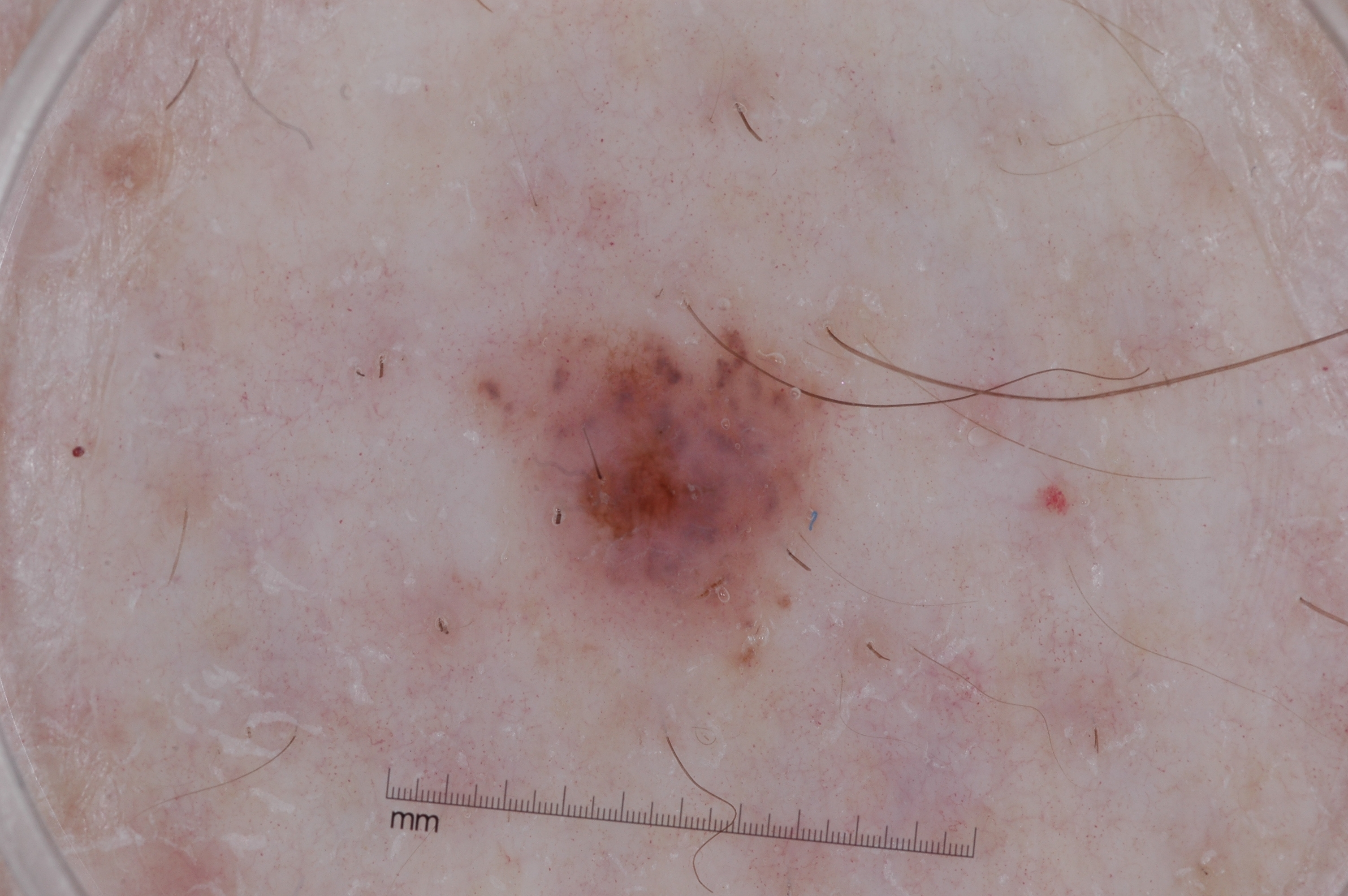The patient is a female aged 58 to 62.
A dermoscopic view of a skin lesion.
Dermoscopically, the lesion shows pigment network, with no streaks, negative network, or milia-like cysts.
The lesion is small relative to the field of view.
With coordinates (x1, y1, x2, y2), the visible lesion spans <bbox>474, 315, 832, 644</bbox>.
The clinical diagnosis was a melanocytic nevus, a benign lesion.